An image taken at a distance: 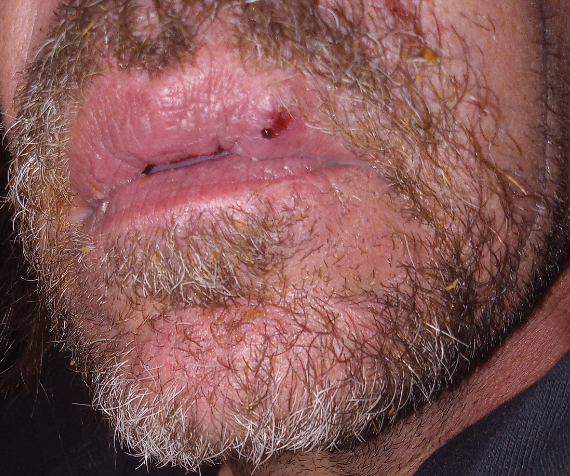Notes:
– assessment · unable to determine